The patient says their skin tans without first burning · dermoscopy of a skin lesion · a female patient aged 75: 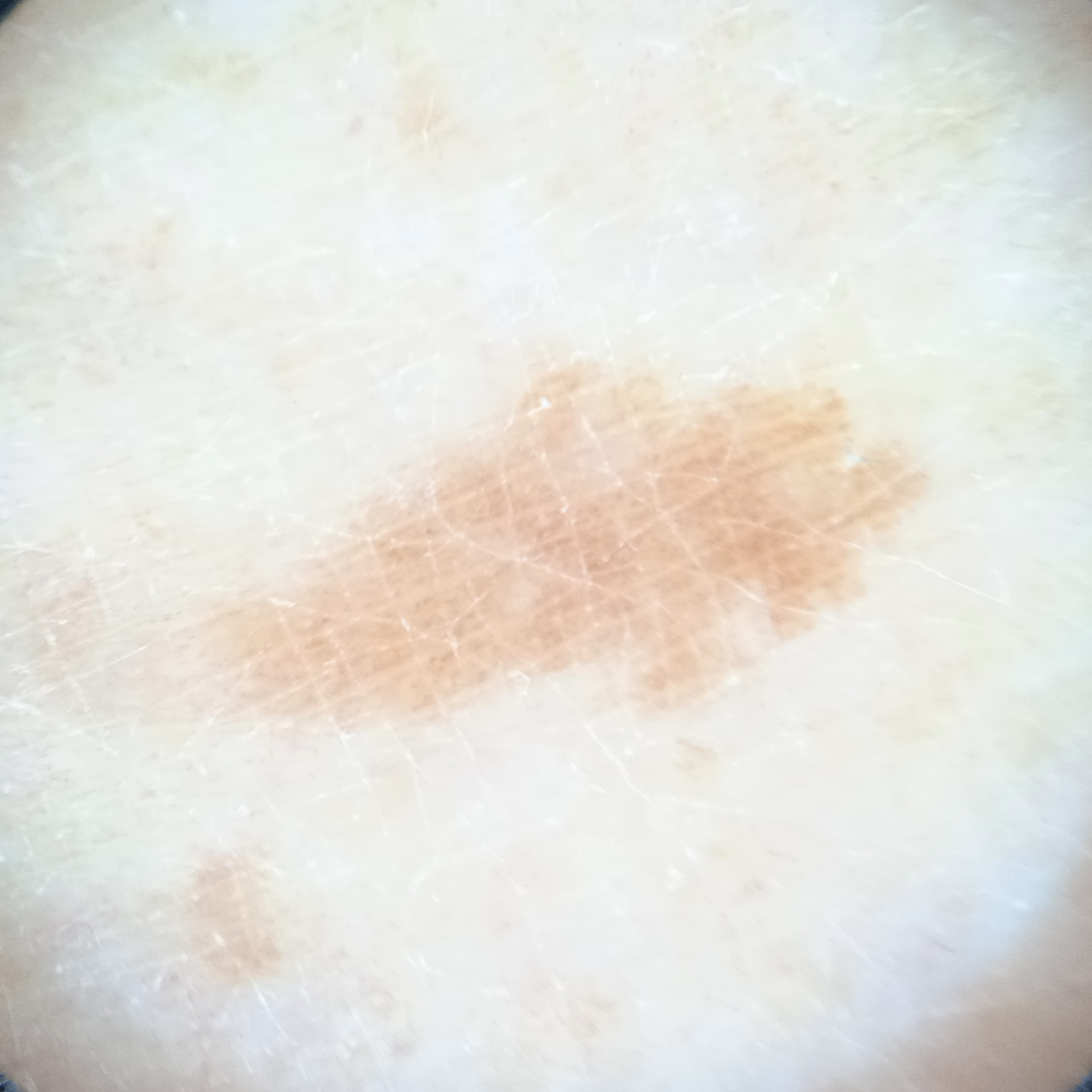The lesion is about 8.2 mm across.
The diagnostic impression was a melanocytic nevus.